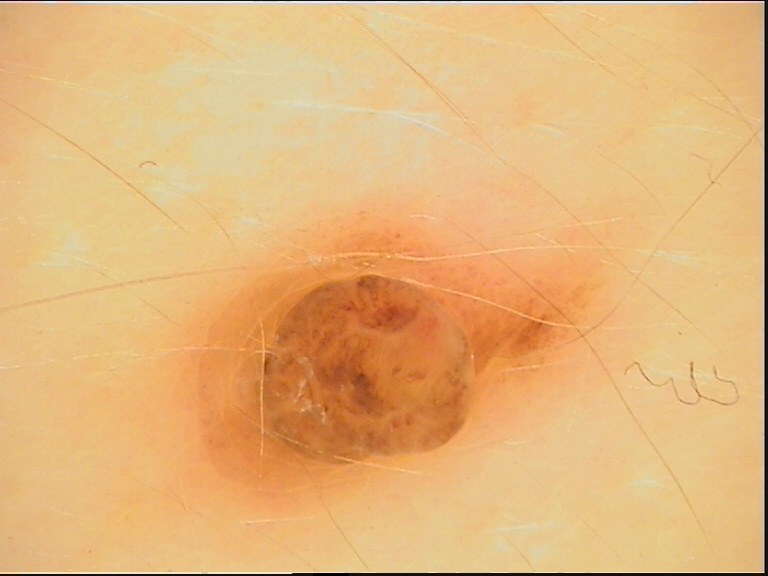Impression: The diagnosis was a dermal nevus.